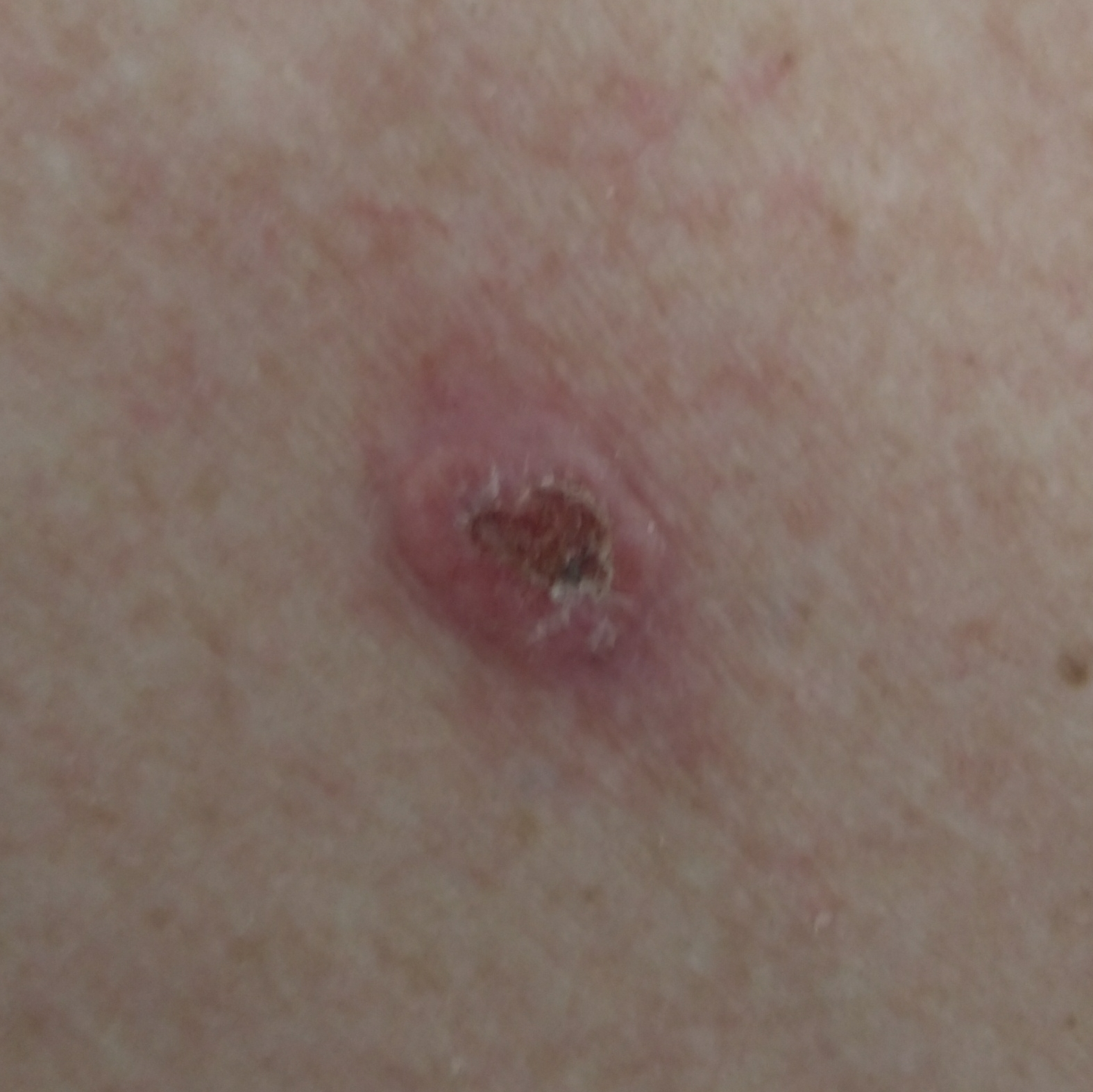The patient was assessed as FST II. A clinical close-up photograph of a skin lesion. A female subject age 52. The chart records pesticide exposure and prior skin cancer (patient or family). The lesion is located on the back. Measuring about 13 × 10 mm. The patient reports that the lesion is elevated, has bled, and itches, but does not hurt. Histopathological examination showed a basal cell carcinoma.